A clinical overview photograph of a skin lesion · a female subject aged 73 to 77 — 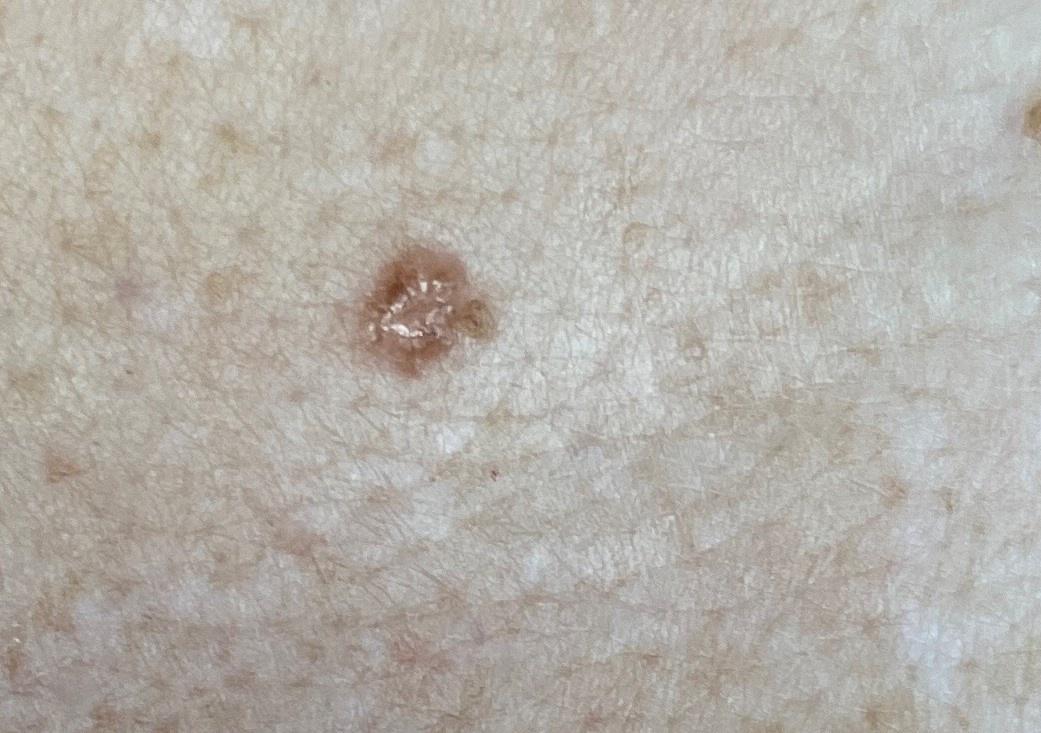site=the trunk | diagnosis=Basal cell carcinoma (biopsy-proven).